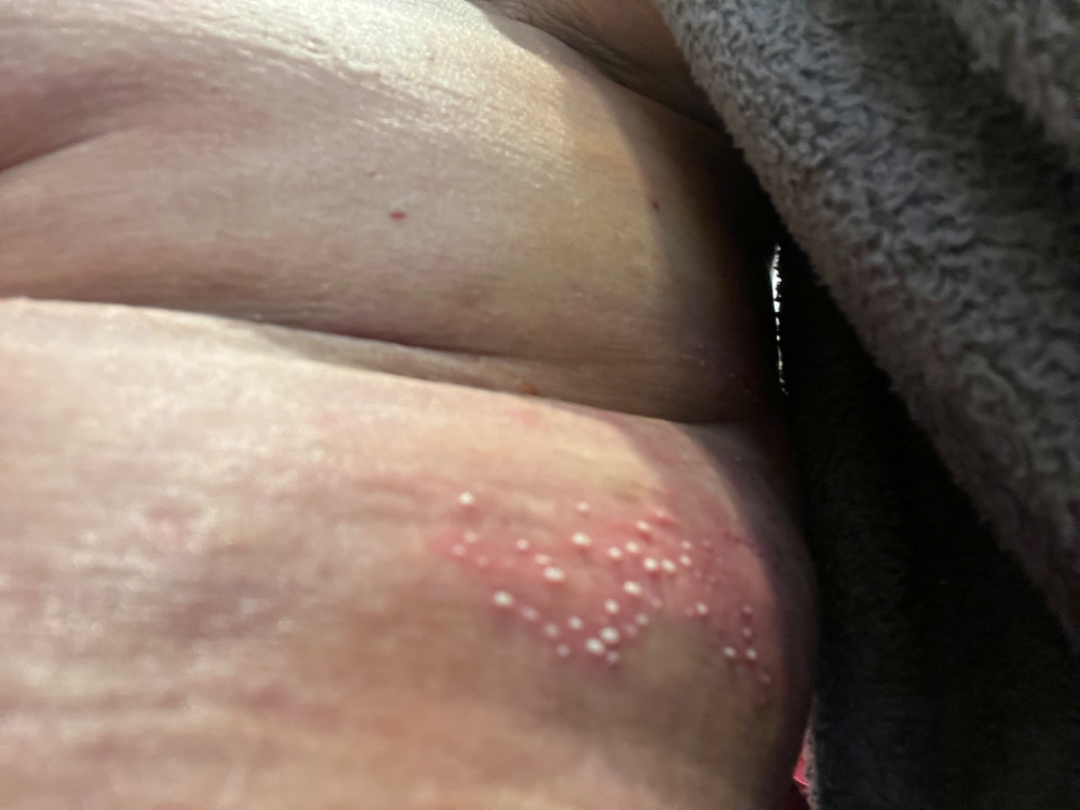The case was difficult to assess from the available photograph.